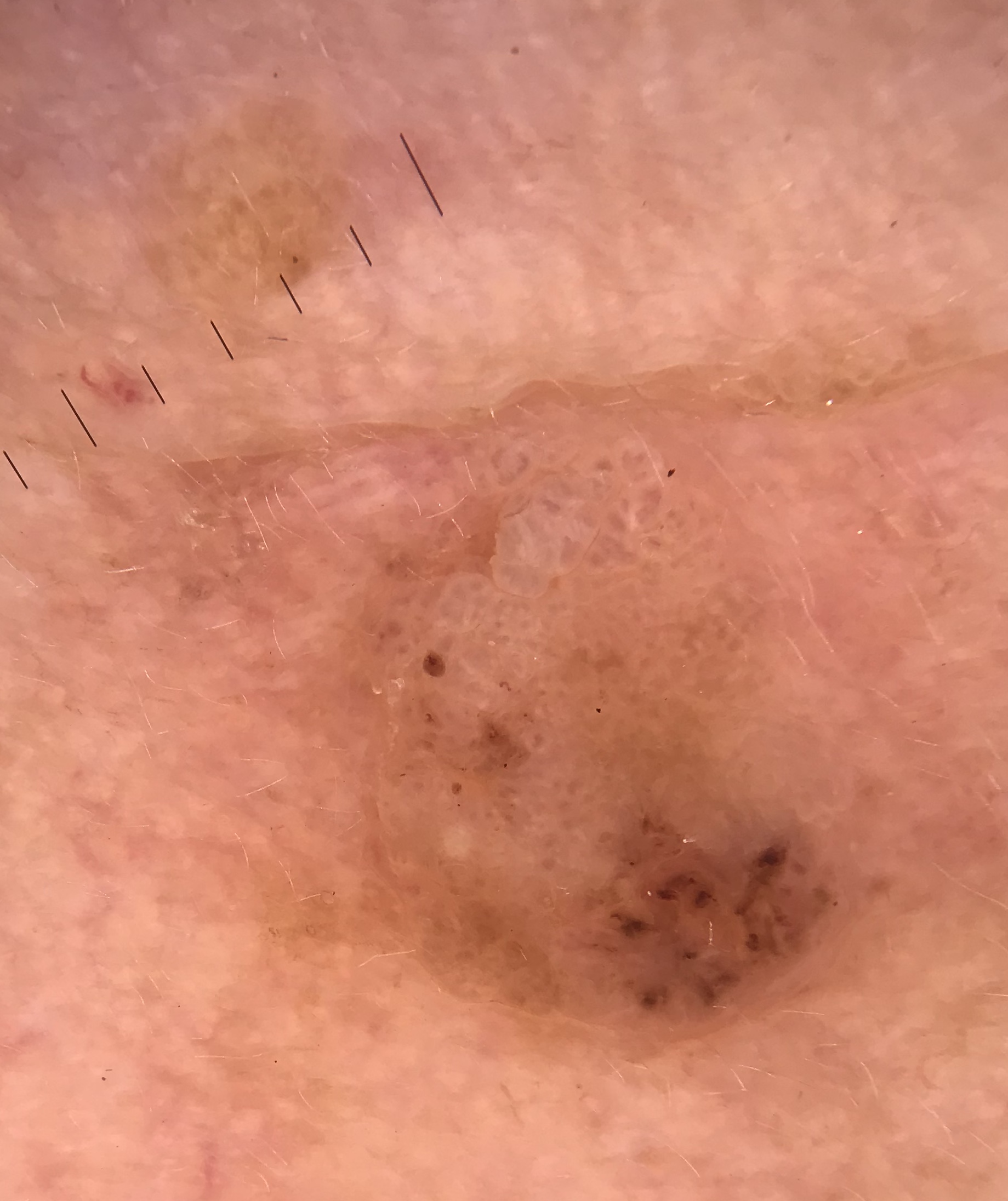classification=keratinocytic; diagnostic label=seborrheic keratosis (expert consensus).